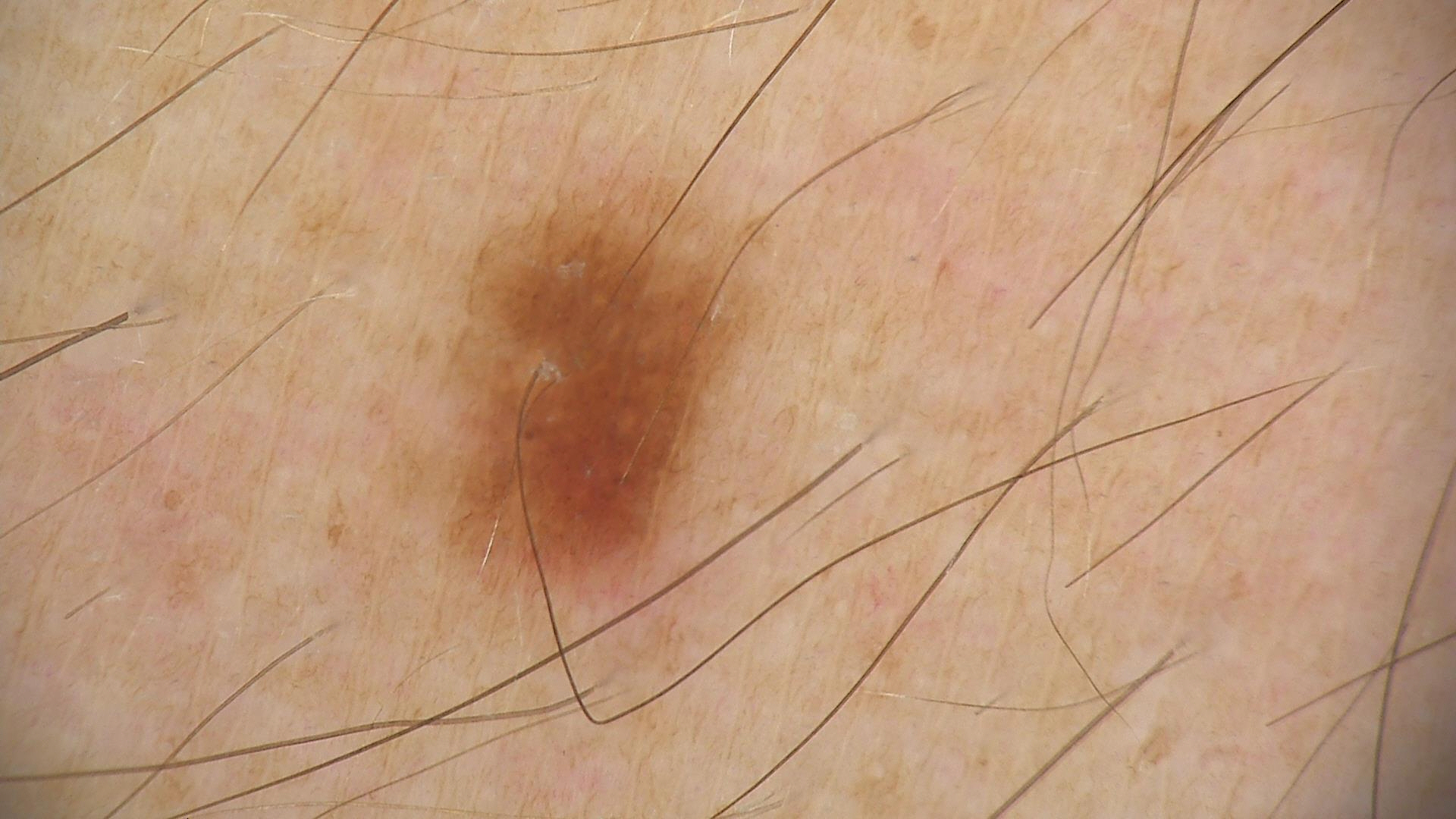A skin lesion imaged with a dermatoscope.
The diagnosis was a dysplastic junctional nevus.